A dermoscopy image of a single skin lesion: 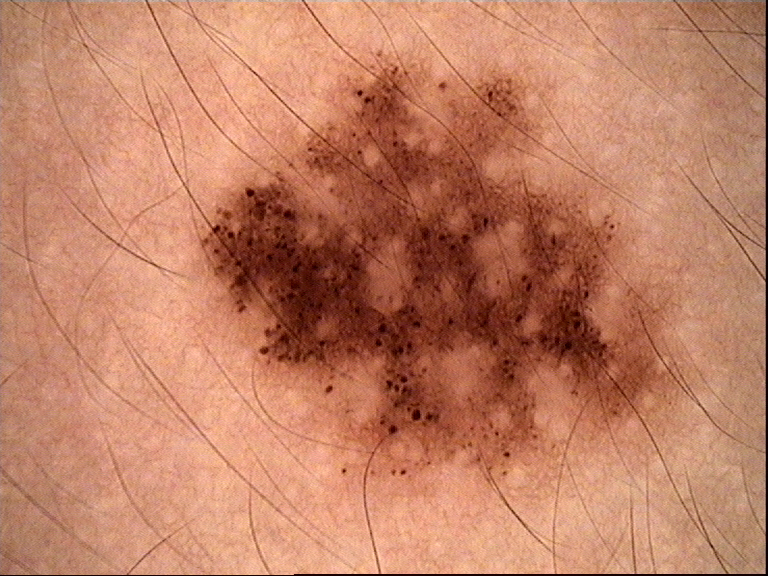Conclusion:
Consistent with a dysplastic junctional nevus.